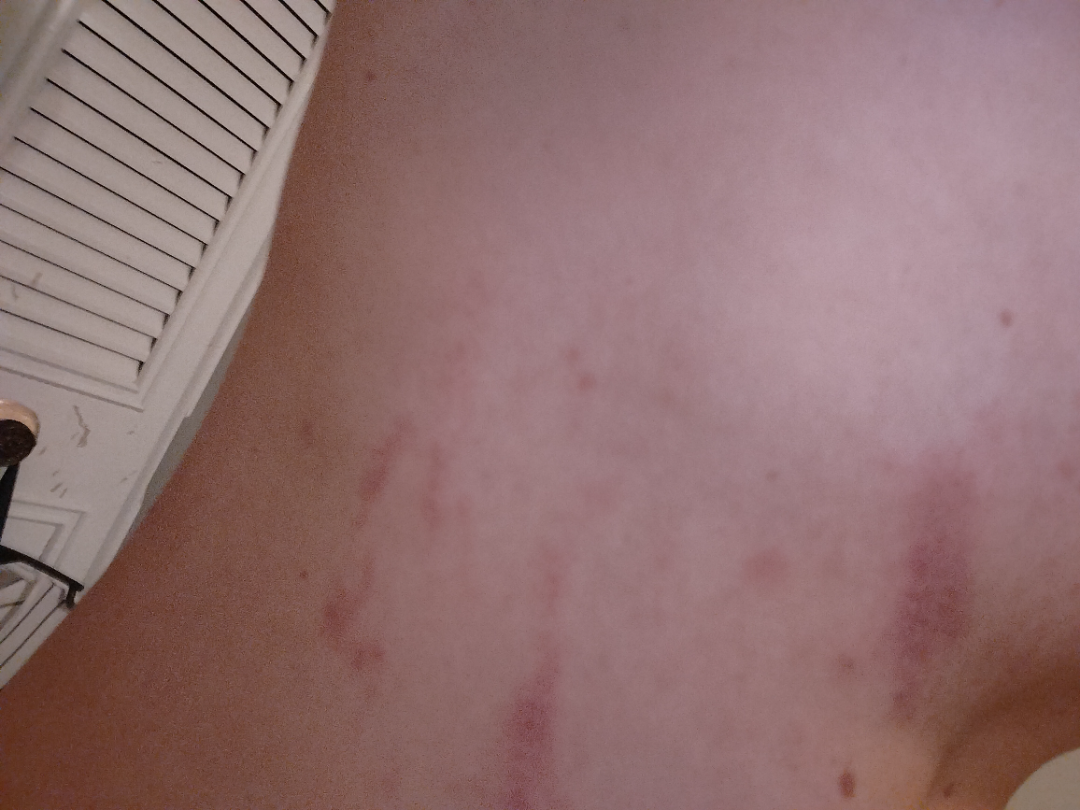assessment: ungradable on photographic review
location: leg and arm
view: close-up